A dermoscopic image of a skin lesion: 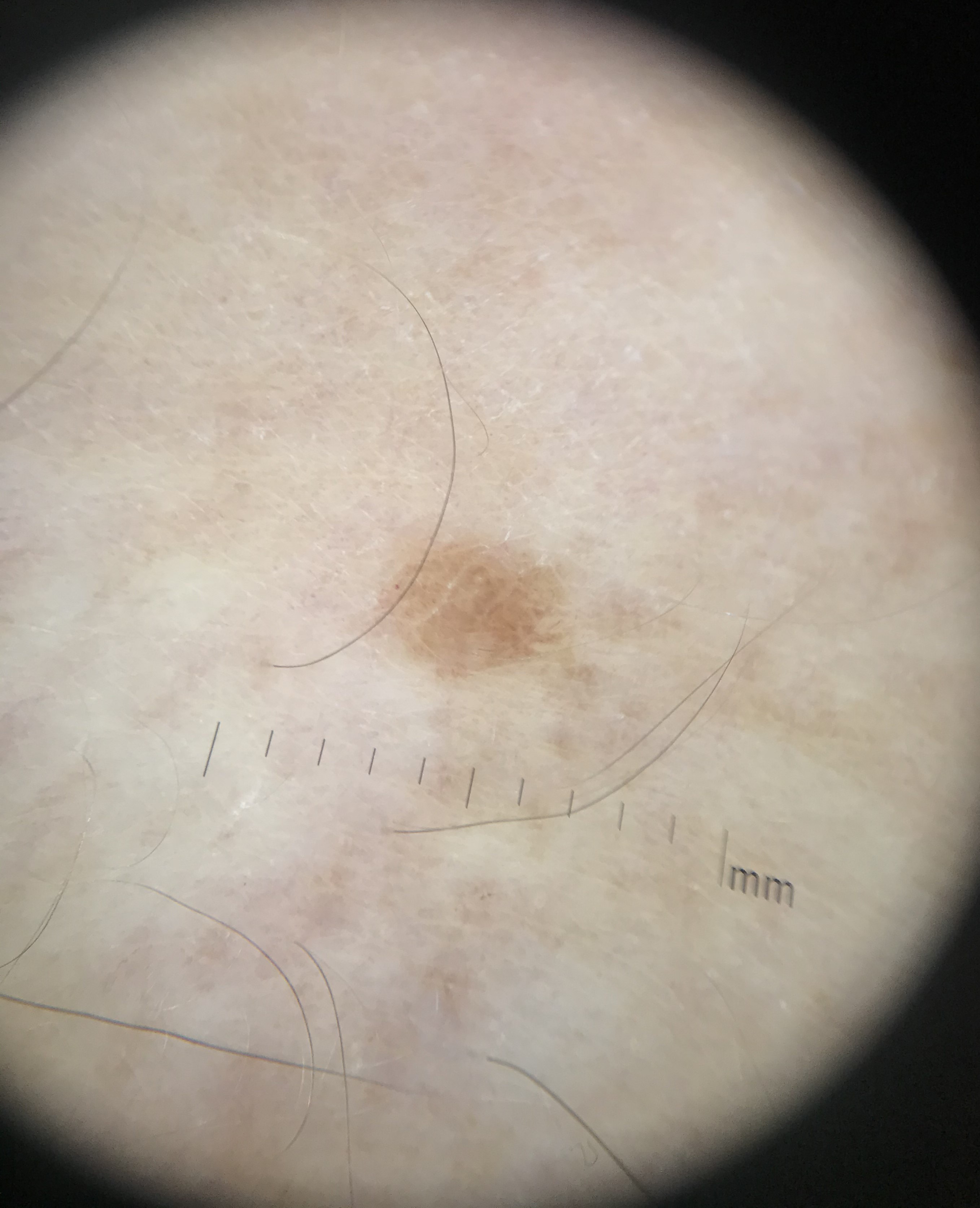| feature | finding |
|---|---|
| subtype | keratinocytic |
| assessment | seborrheic keratosis (expert consensus) |